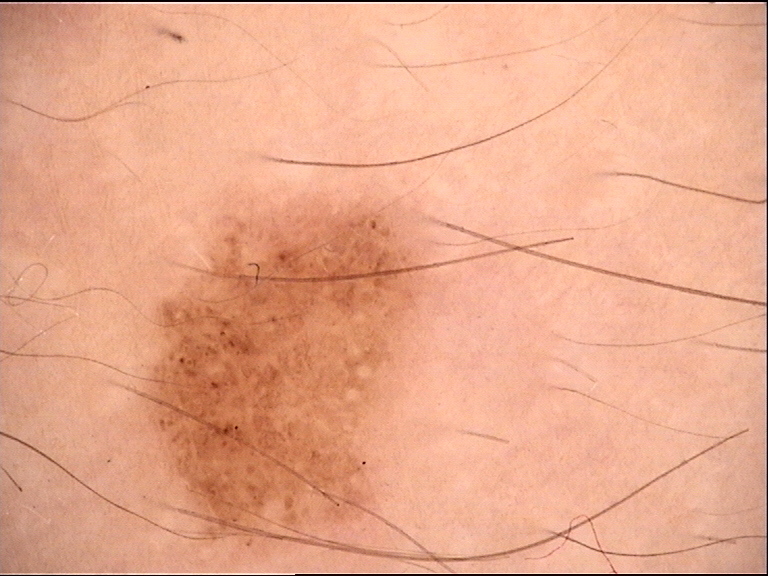This is a banal lesion.
Consistent with a junctional nevus.